A dermatoscopic image of a skin lesion.
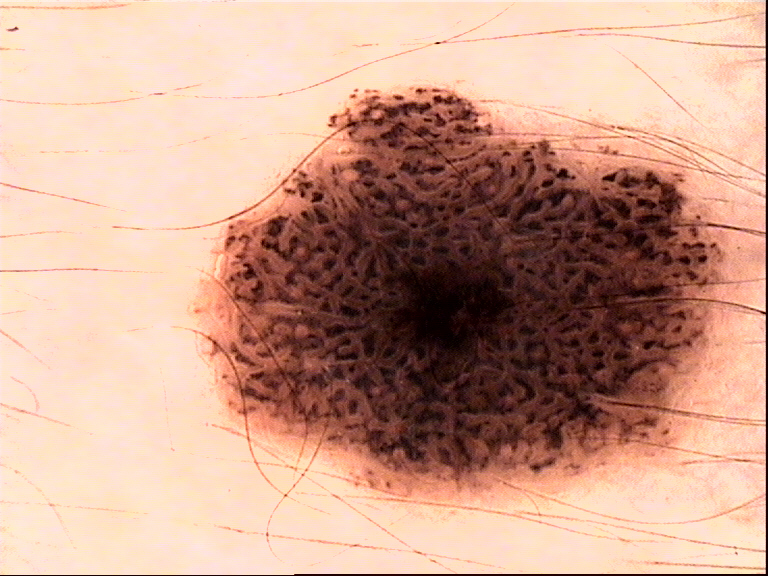subtype — keratinocytic
assessment — seborrheic keratosis (expert consensus)